A dermatoscopic image of a skin lesion:
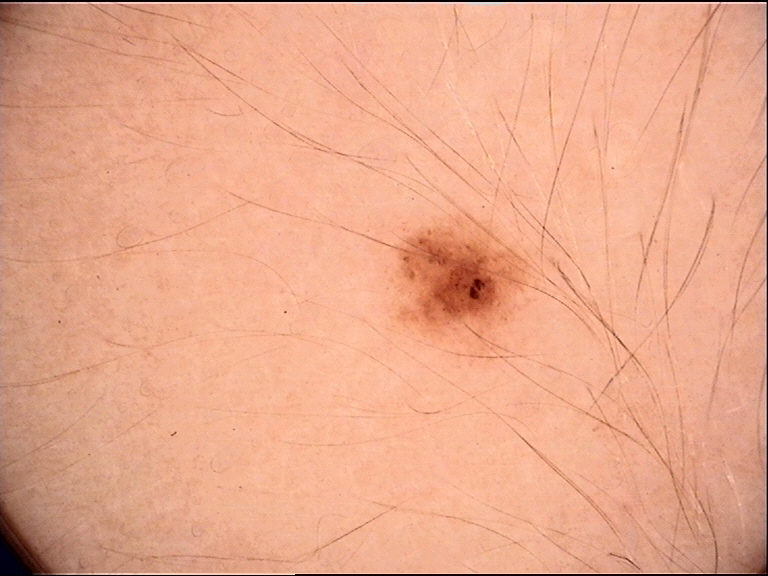The diagnosis was a benign lesion — a dysplastic junctional nevus.